The contributor reports the condition has been present for one to three months. The patient described the issue as a rash. The patient is male. The arm is involved. A close-up photograph. The lesion is described as raised or bumpy and fluid-filled. FST III; non-clinician graders estimated 4 on the Monk Skin Tone — 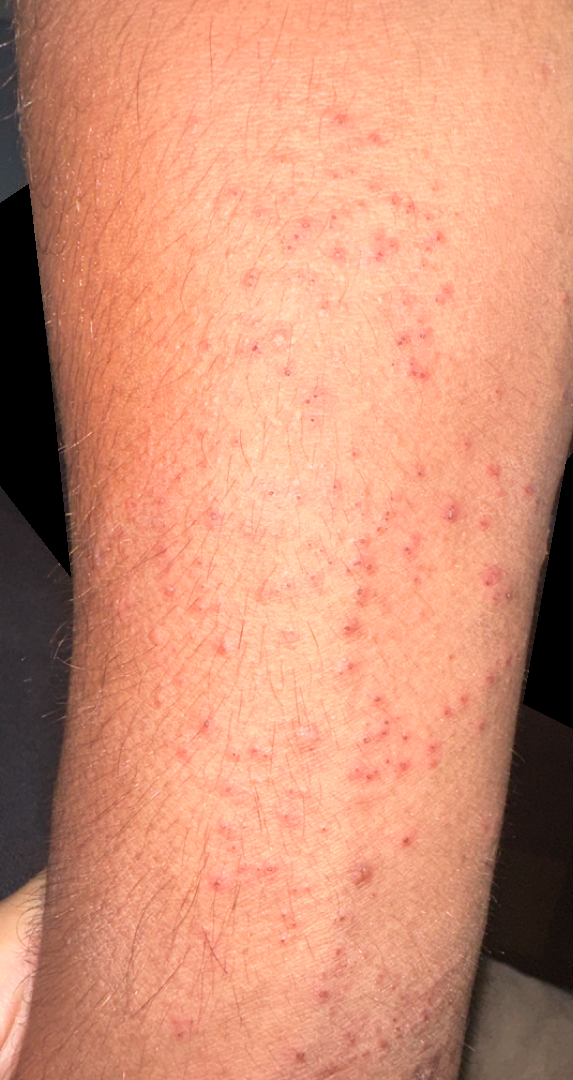{
  "differential": {
    "Eczema": 0.35,
    "Acute dermatitis, NOS": 0.26,
    "Allergic Contact Dermatitis": 0.26,
    "Lichen planus/lichenoid eruption": 0.13
  }
}